The photograph was taken at a distance. The affected area is the leg:
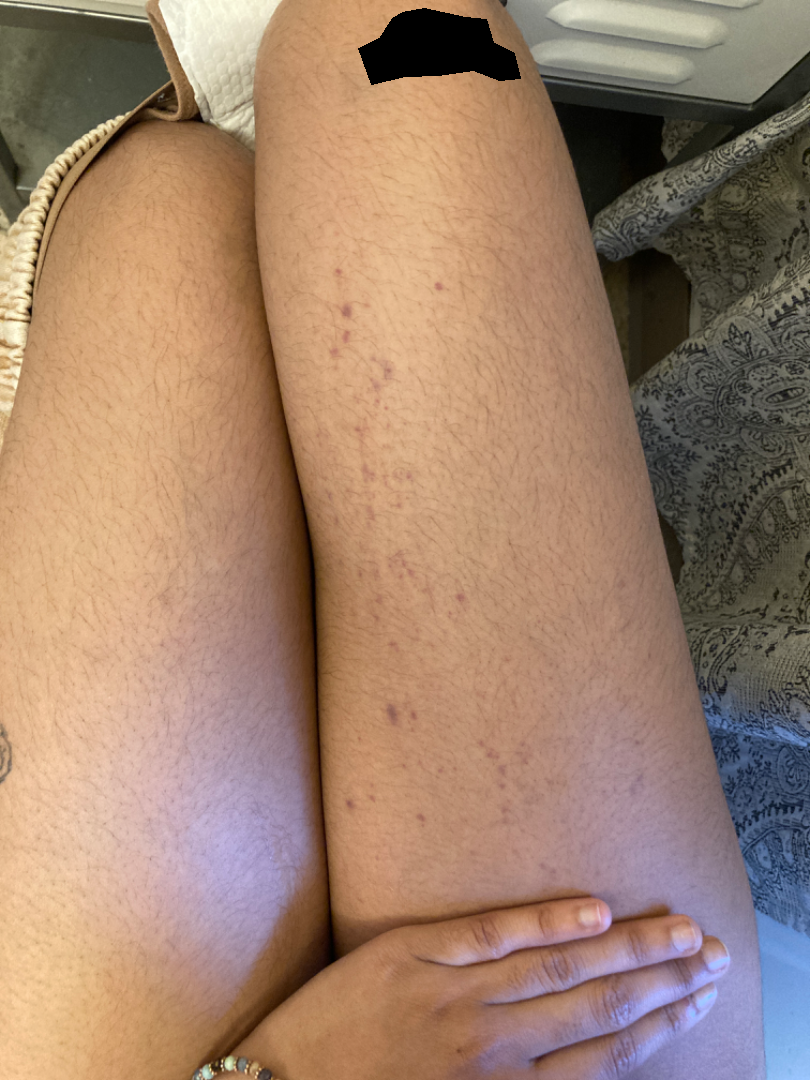surface texture = flat | patient-reported symptoms = enlargement, darkening and itching | symptom duration = about one day | constitutional symptoms = none reported | differential diagnosis = a single dermatologist reviewed the case: Contact purpura, Lichen planus/lichenoid eruption and Pigmented purpuric eruption were each considered, in no particular order.